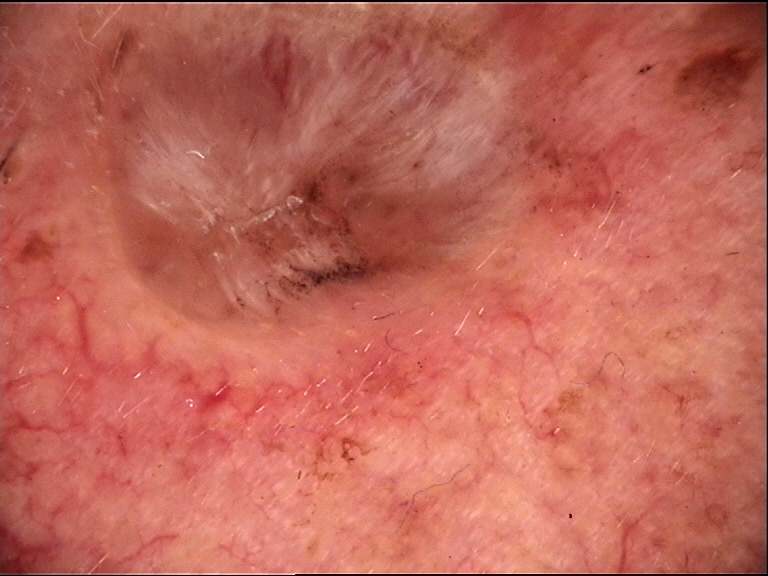A skin lesion imaged with a dermatoscope. Biopsy-confirmed as a keratinocytic lesion — a basal cell carcinoma.